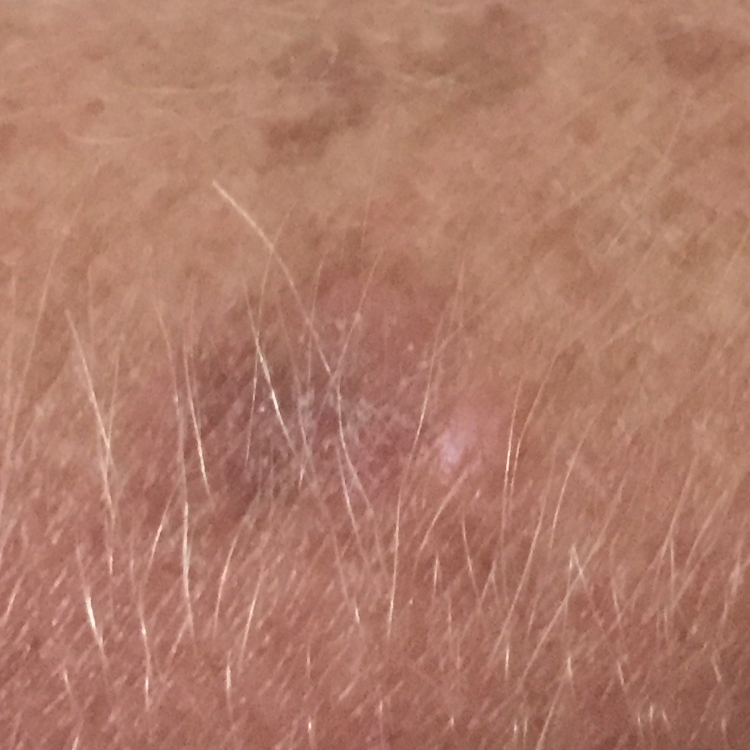Findings: A smartphone photograph of a skin lesion. A subject in their early 40s. The lesion involves a forearm. The patient reports that the lesion itches, but has not grown and has not bled. Conclusion: The consensus clinical diagnosis was an actinic keratosis.